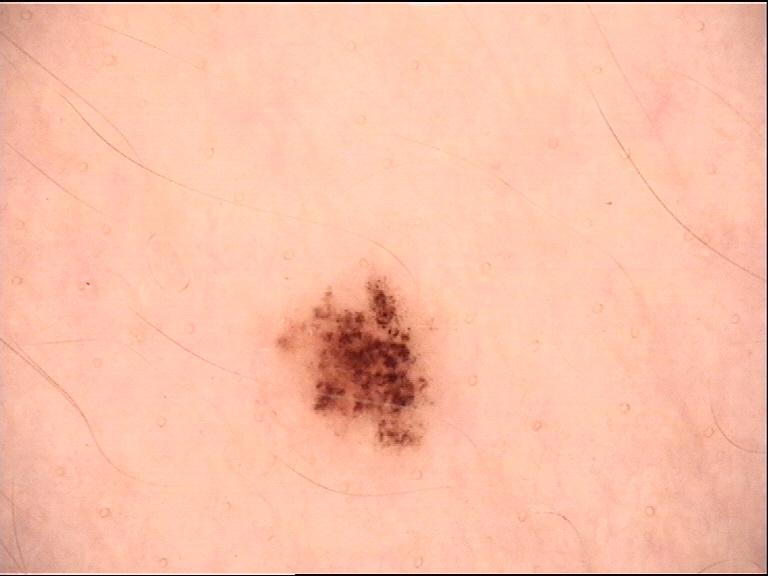A dermoscopy image of a single skin lesion. Consistent with a benign lesion — a dysplastic junctional nevus.